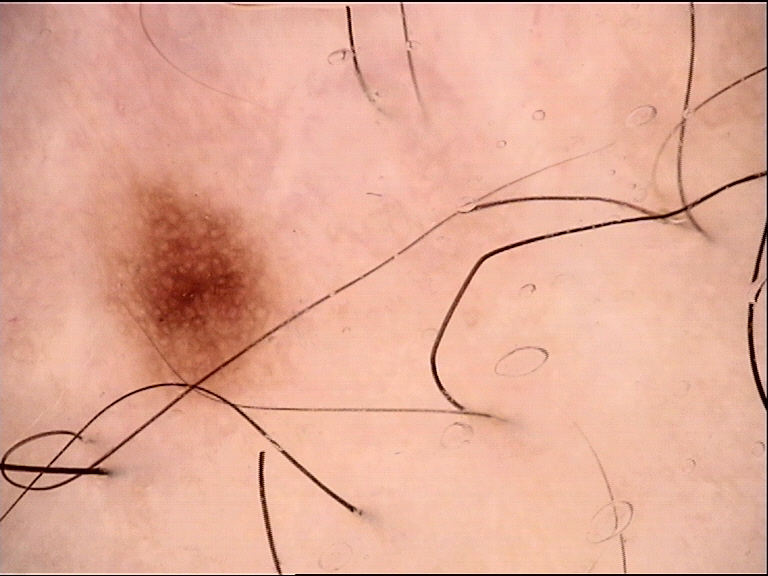Consistent with a dysplastic junctional nevus.